The subject is a male approximately 50 years of age, a dermatoscopic image of a skin lesion.
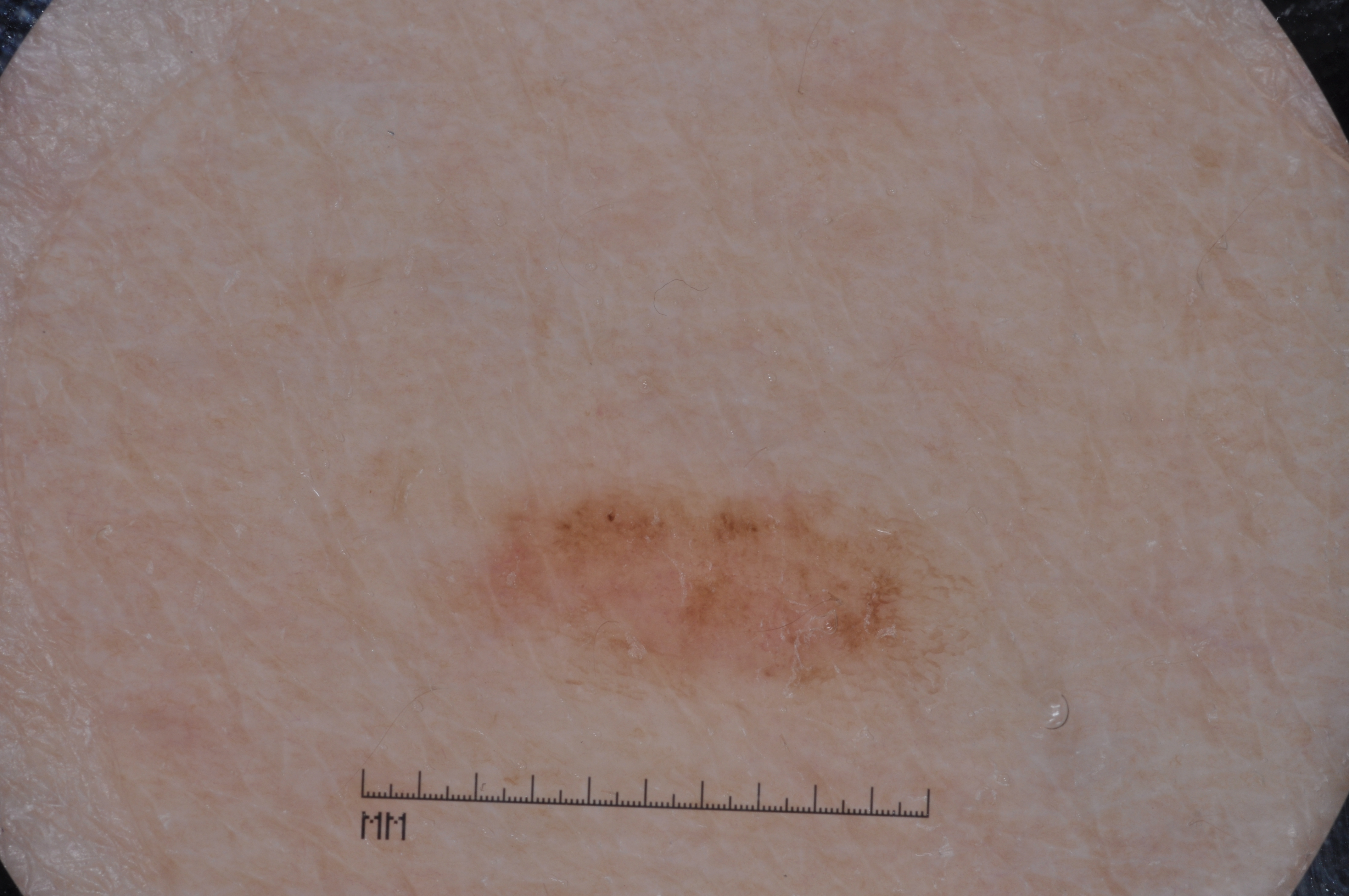Case summary:
* lesion extent · ~6% of the field
* features · pigment network; absent: streaks, negative network, and milia-like cysts
* lesion location · [464, 483, 938, 686]
* assessment · a melanocytic nevus, a benign skin lesion